A smartphone photograph of a skin lesion · a female patient aged 53 · skin type II · history notes prior skin cancer (patient or family) and no tobacco use.
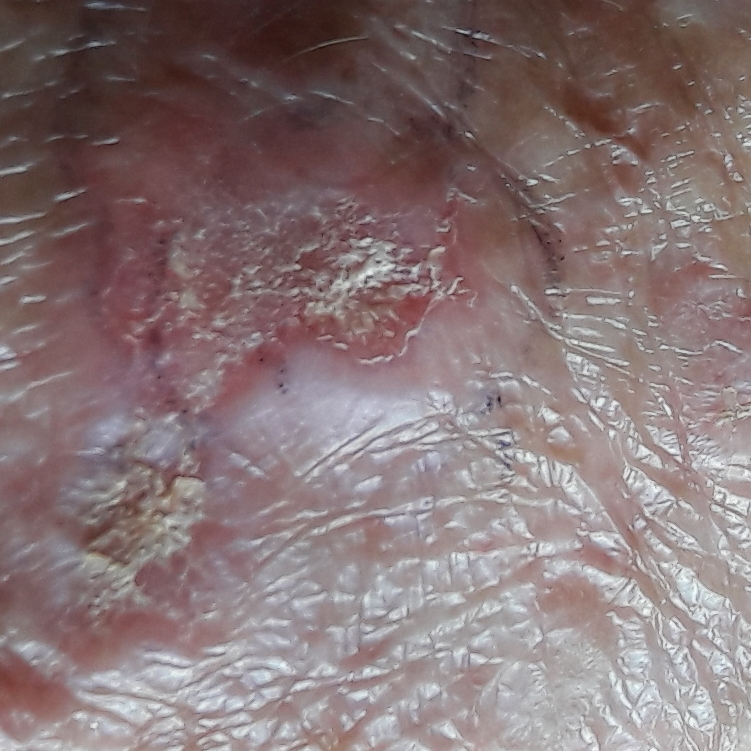<case>
  <lesion_location>a hand</lesion_location>
  <symptoms>
    <present>pain, itching, bleeding, elevation, growth</present>
  </symptoms>
  <diagnosis>
    <name>basal cell carcinoma</name>
    <code>BCC</code>
    <malignancy>malignant</malignancy>
    <confirmation>histopathology</confirmation>
  </diagnosis>
</case>